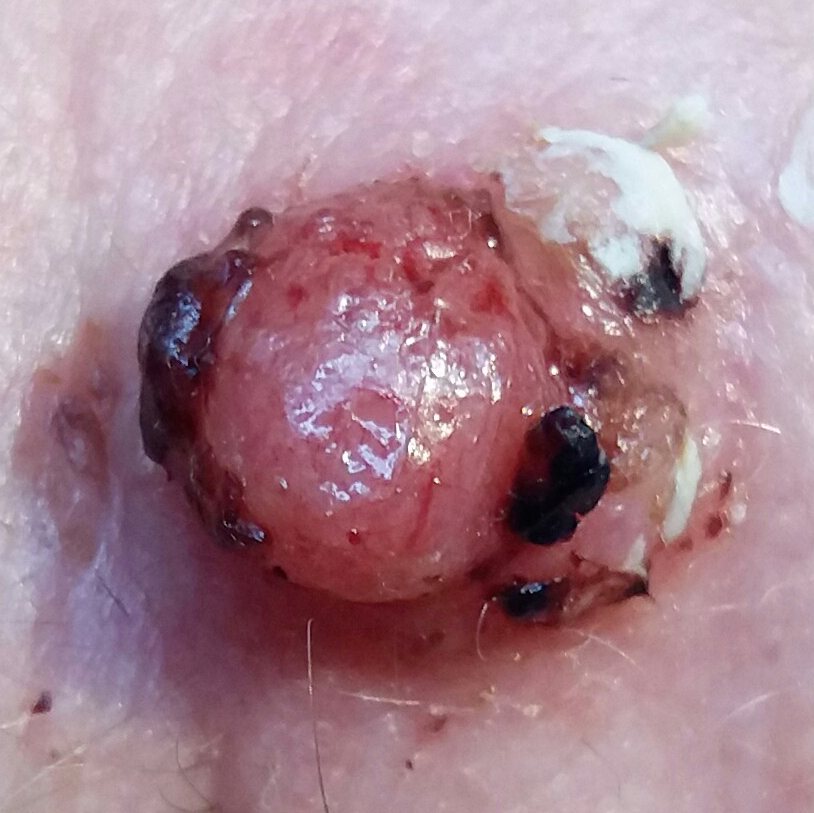{
  "lesion_location": "the face",
  "lesion_size": {
    "diameter_1_mm": 12.0,
    "diameter_2_mm": 10.0
  },
  "symptoms": {
    "present": [
      "itching",
      "elevation",
      "bleeding",
      "growth",
      "change in appearance"
    ],
    "absent": [
      "pain"
    ]
  },
  "diagnosis": {
    "name": "squamous cell carcinoma",
    "code": "SCC",
    "malignancy": "malignant",
    "confirmation": "histopathology"
  }
}